A dermoscopic photograph of a skin lesion.
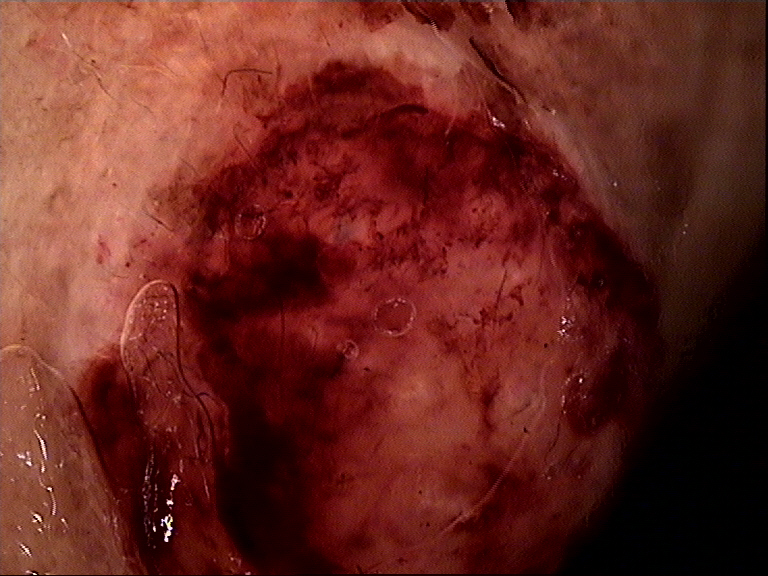diagnosis = squamous cell carcinoma (biopsy-proven).